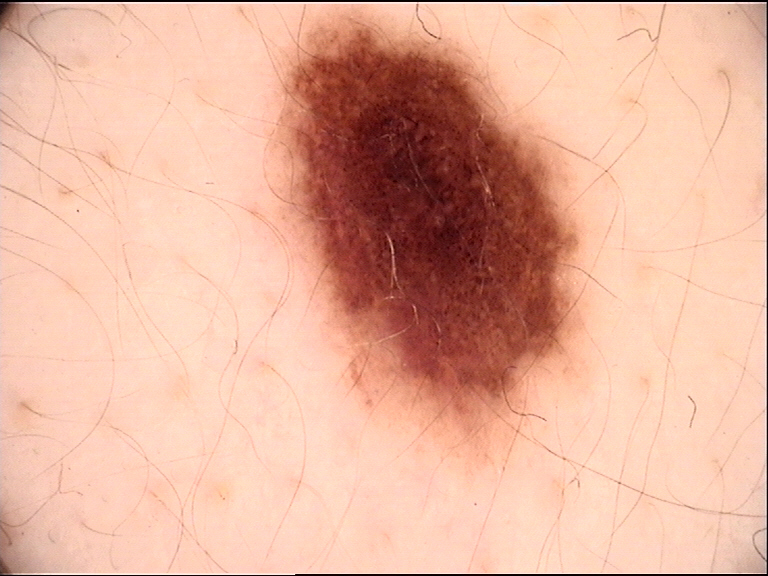modality = dermoscopy | diagnosis = dysplastic compound nevus (expert consensus).